A dermoscopy image of a single skin lesion: 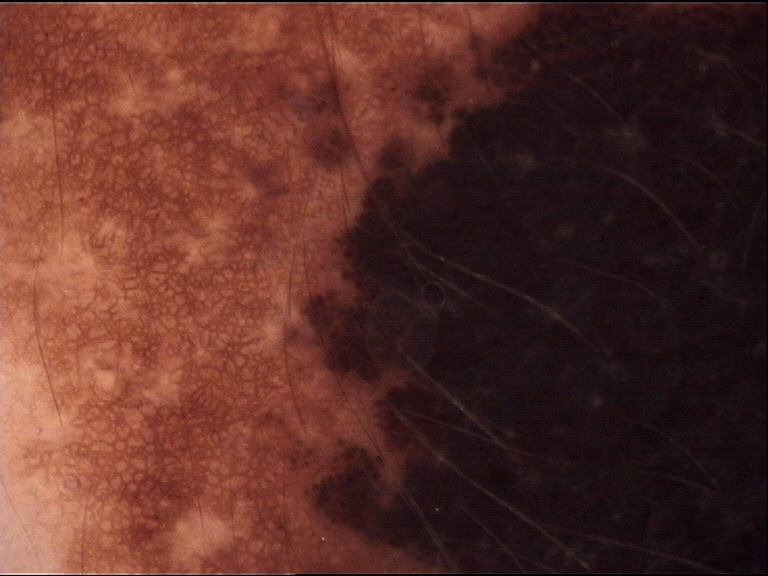Case: The morphology is that of a banal lesion. Impression: Diagnosed as a congenital compound nevus.